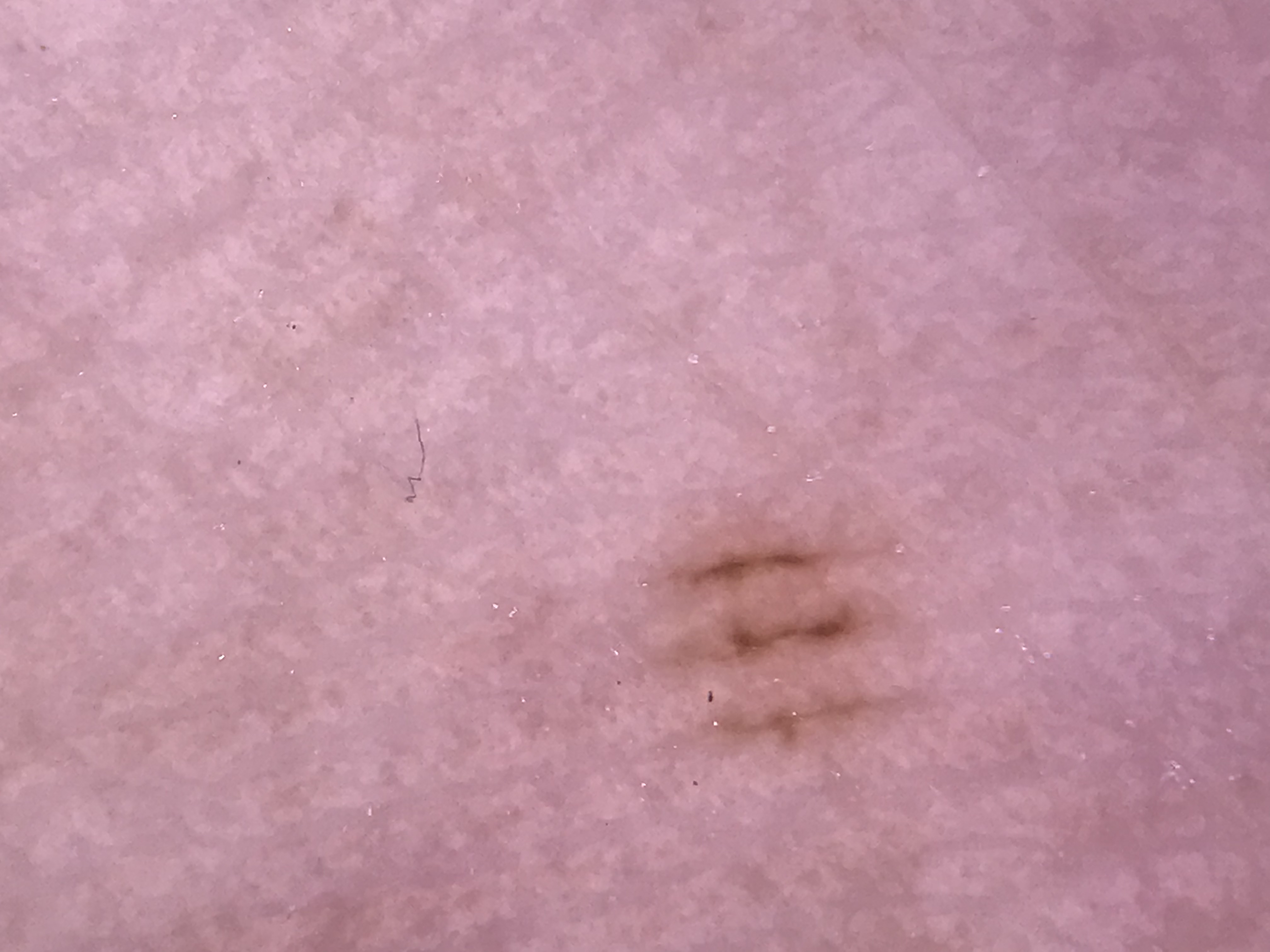Classified as a banal lesion — an acral junctional nevus.